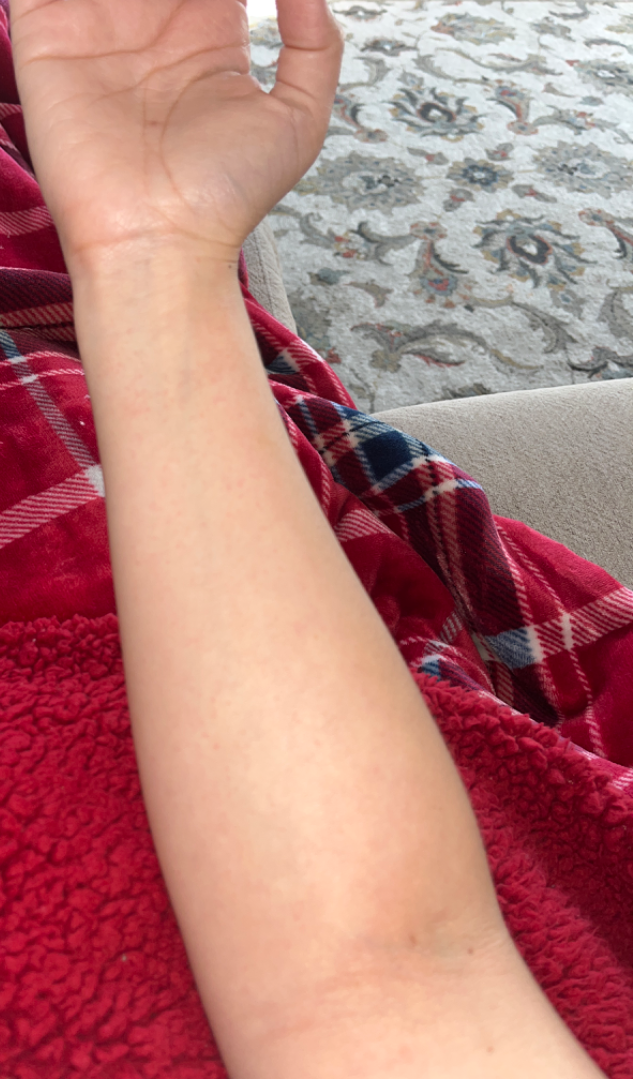– differential diagnosis · single-reviewer assessment: the primary impression is Irritant Contact Dermatitis; an alternative is Acute dermatitis, NOS